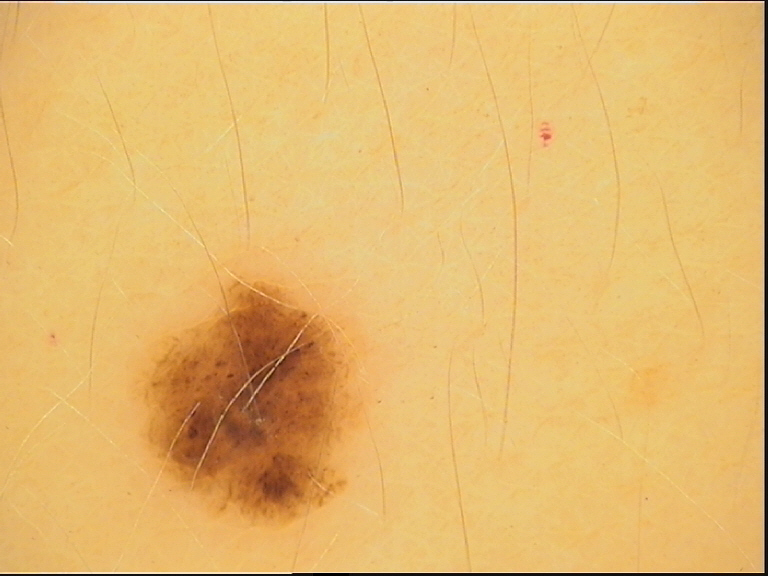The diagnostic label was a dysplastic compound nevus.